FST III; human graders estimated a MST of 3 · the lesion involves the leg · the photograph was taken at a distance · the patient indicates the lesion is raised or bumpy · the patient considered this a rash · present for one to three months · symptoms reported: bothersome appearance and itching.
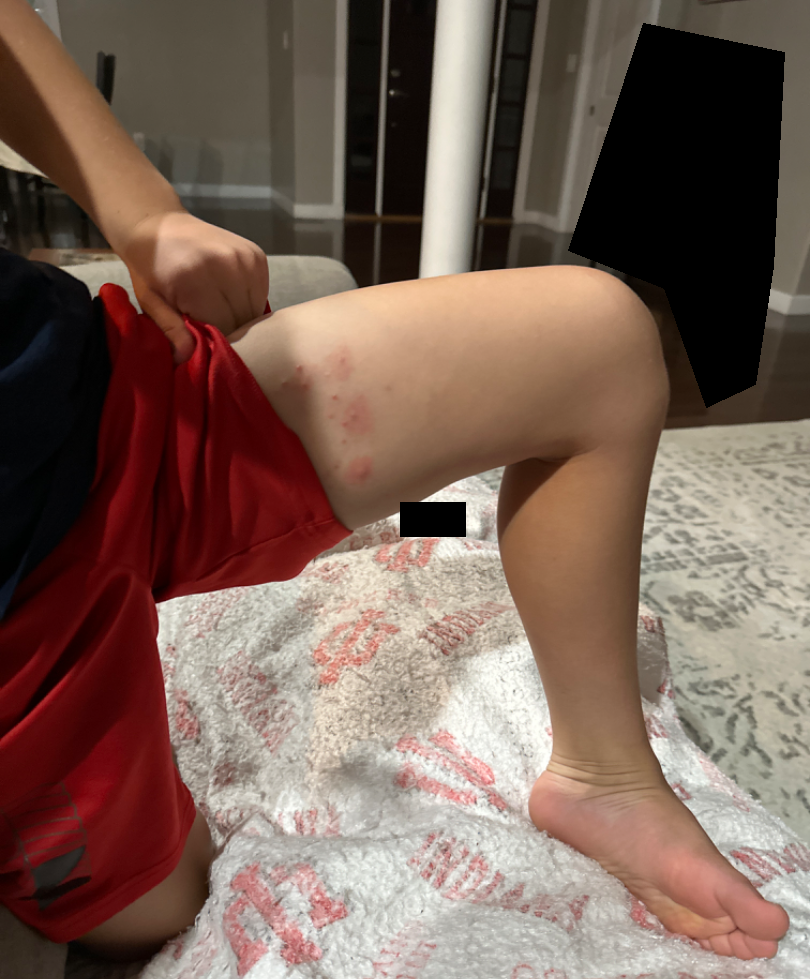| key | value |
|---|---|
| assessment | most consistent with Molluscum Contagiosum |